The photograph is a close-up of the affected area:
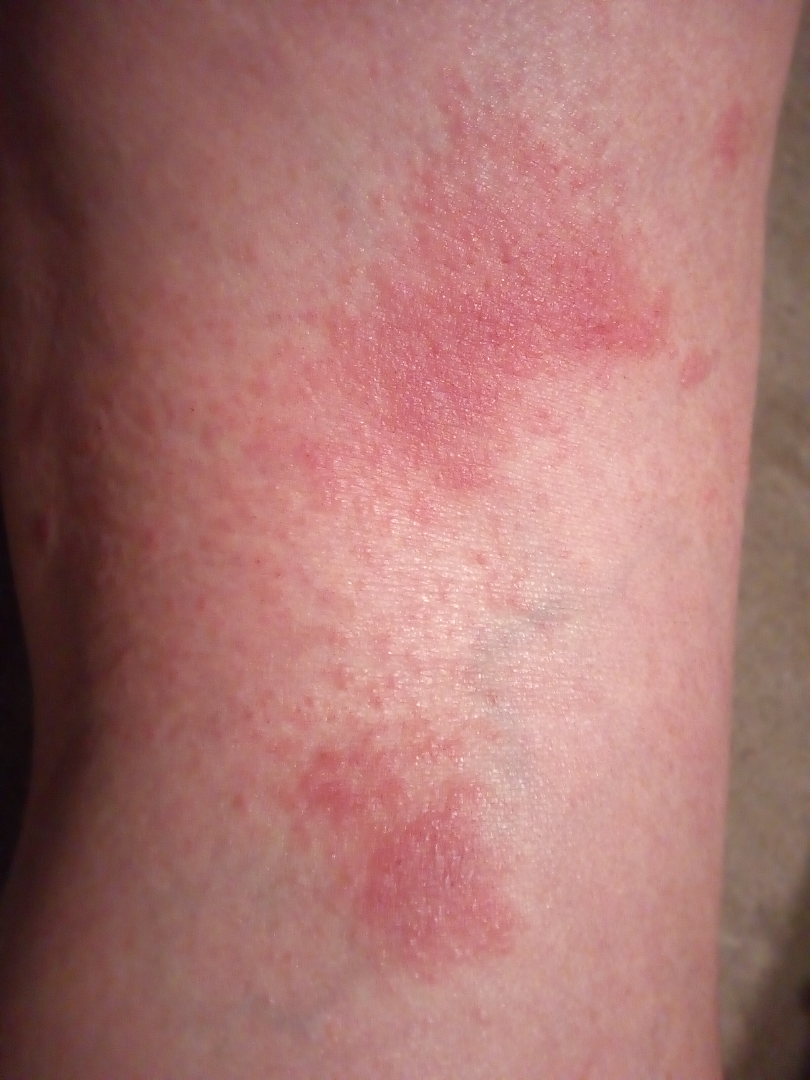Eczema (0.67); Allergic Contact Dermatitis (0.33).